The photograph is a close-up of the affected area: 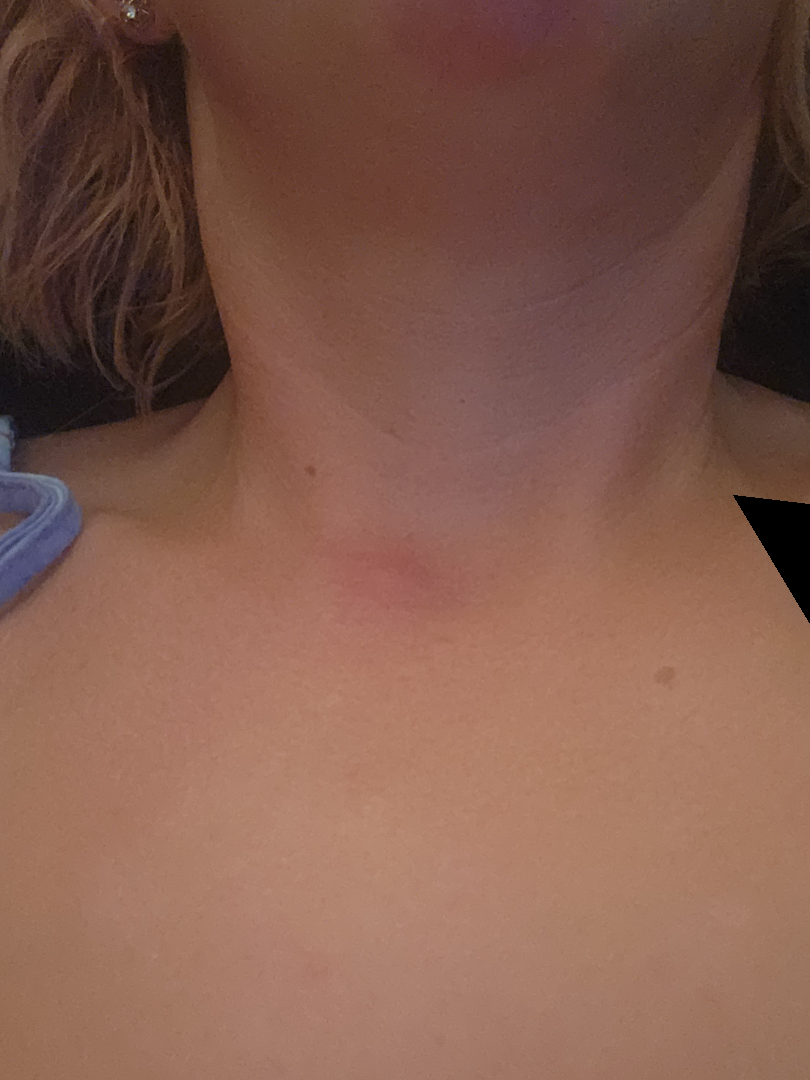  differential:
    leading:
      - Insect Bite
    considered:
      - Cyst